A dermoscopy image of a single skin lesion: 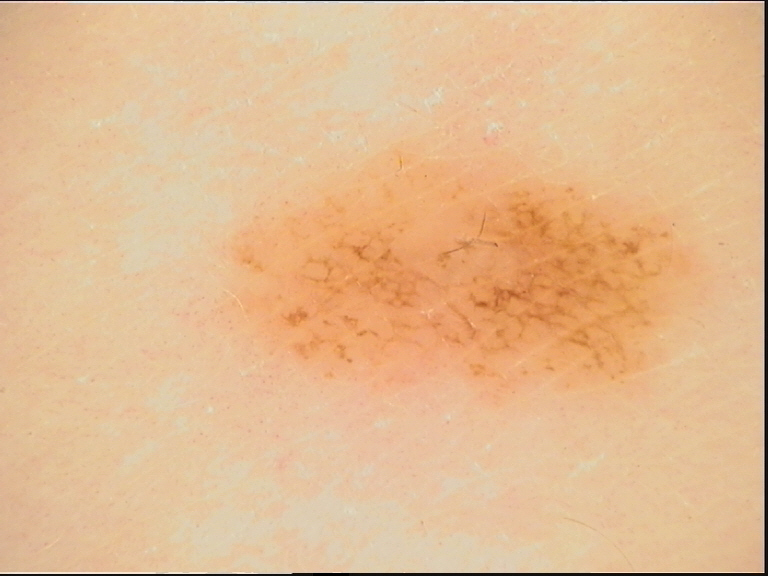Classified as a dysplastic junctional nevus.